A dermoscopic photograph of a skin lesion: 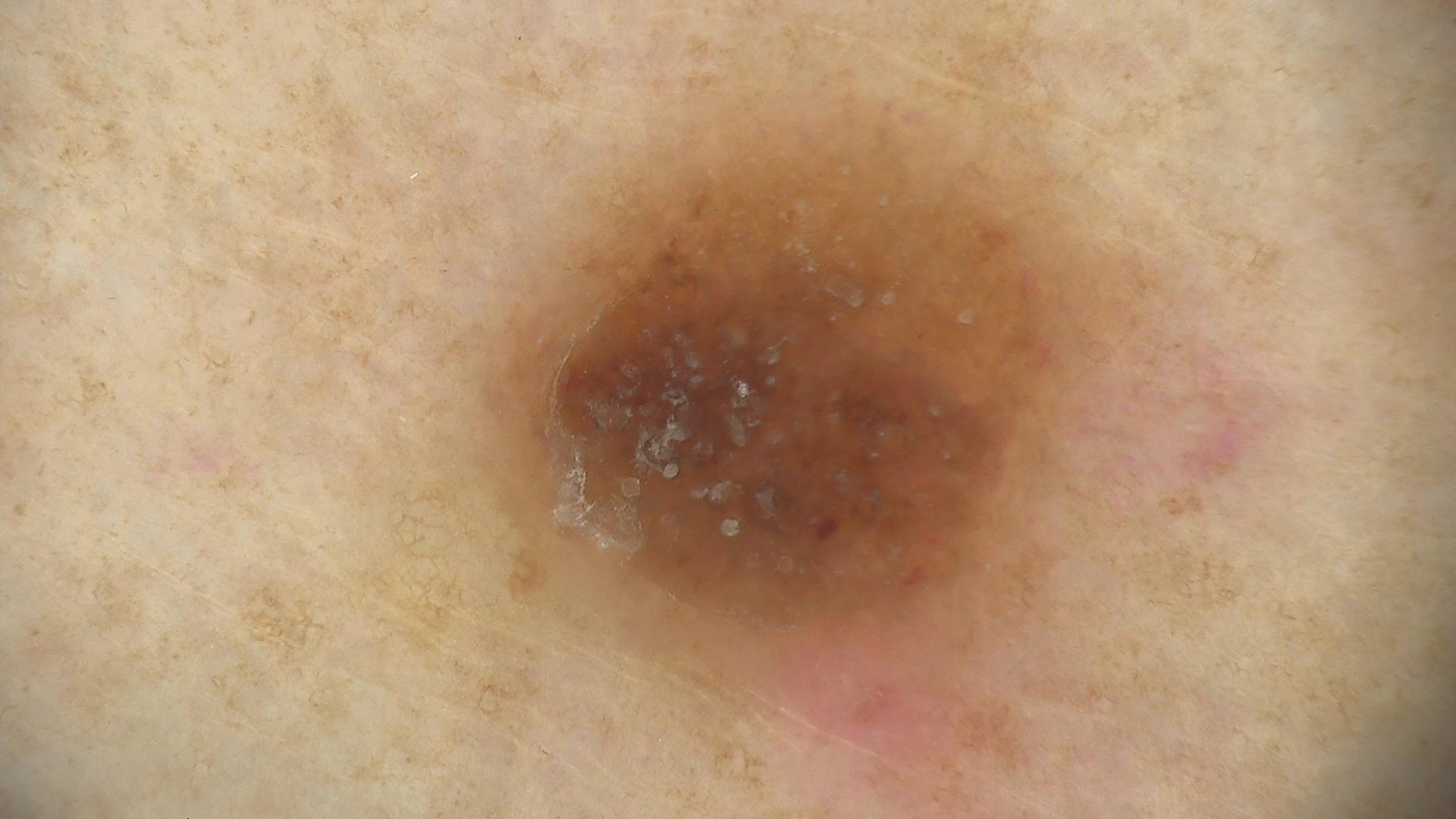{
  "lesion_type": {
    "main_class": "keratinocytic"
  },
  "diagnosis": {
    "name": "seborrheic keratosis",
    "code": "sk",
    "malignancy": "benign",
    "super_class": "non-melanocytic",
    "confirmation": "expert consensus"
  }
}